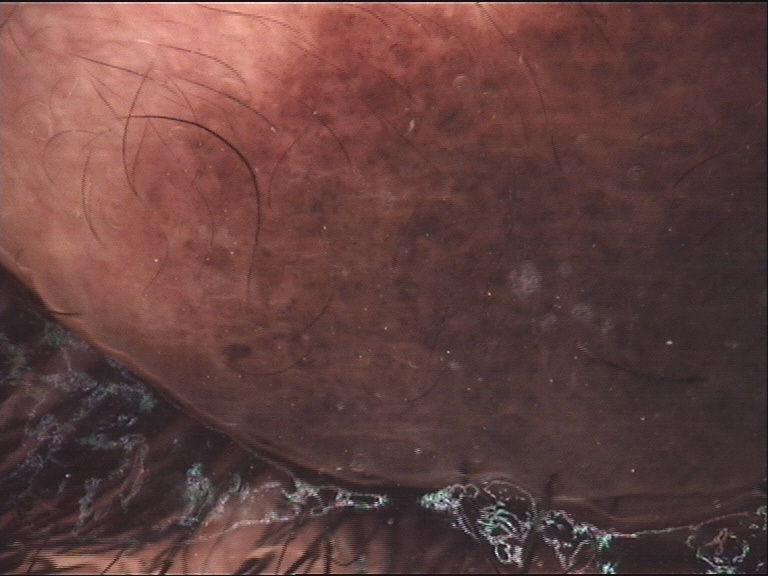- subtype · banal
- class · congenital compound nevus (expert consensus)